A clinical photo of a skin lesion taken with a smartphone. The chart notes alcohol use, pesticide exposure, and prior skin cancer (patient or family). Recorded as skin type II. A male subject 62 years of age: 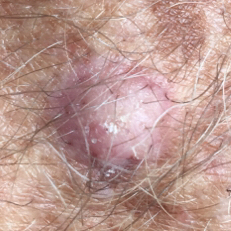Case summary: The lesion was found on a forearm. Measuring about 8 × 7 mm. Per patient report, the lesion is elevated, but does not itch and has not changed. Conclusion: Histopathological examination showed a lesion of indeterminate malignant potential — an actinic keratosis.